The affected area is the leg; the patient reported no systemic symptoms; the contributor is male; this is a close-up image; Fitzpatrick skin type IV; the lesion is described as raised or bumpy; the patient described the issue as a rash — 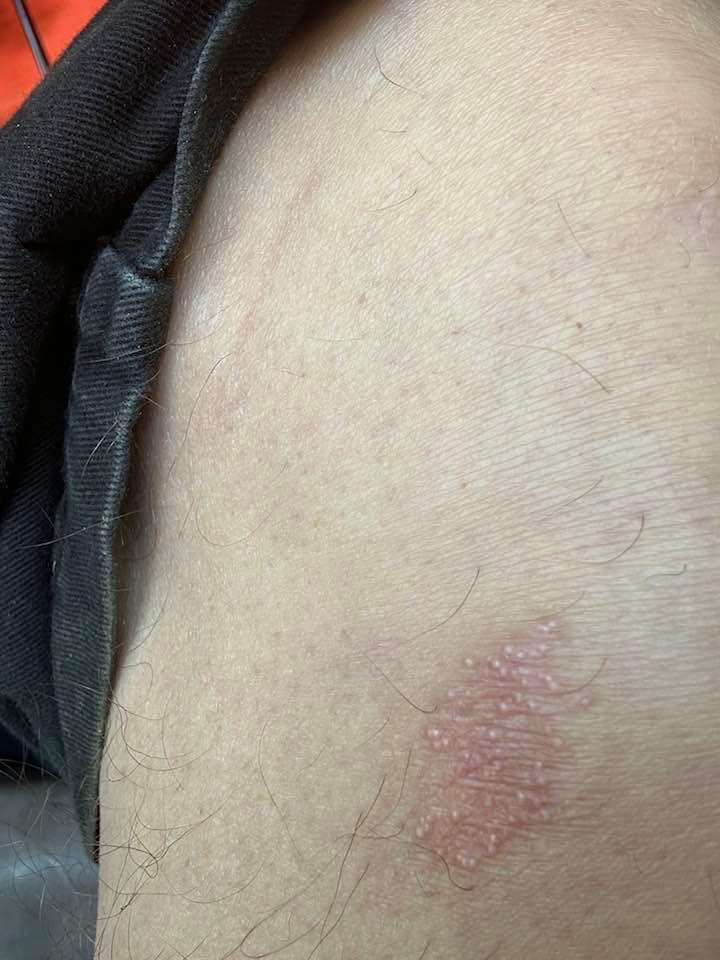  assessment: could not be assessed